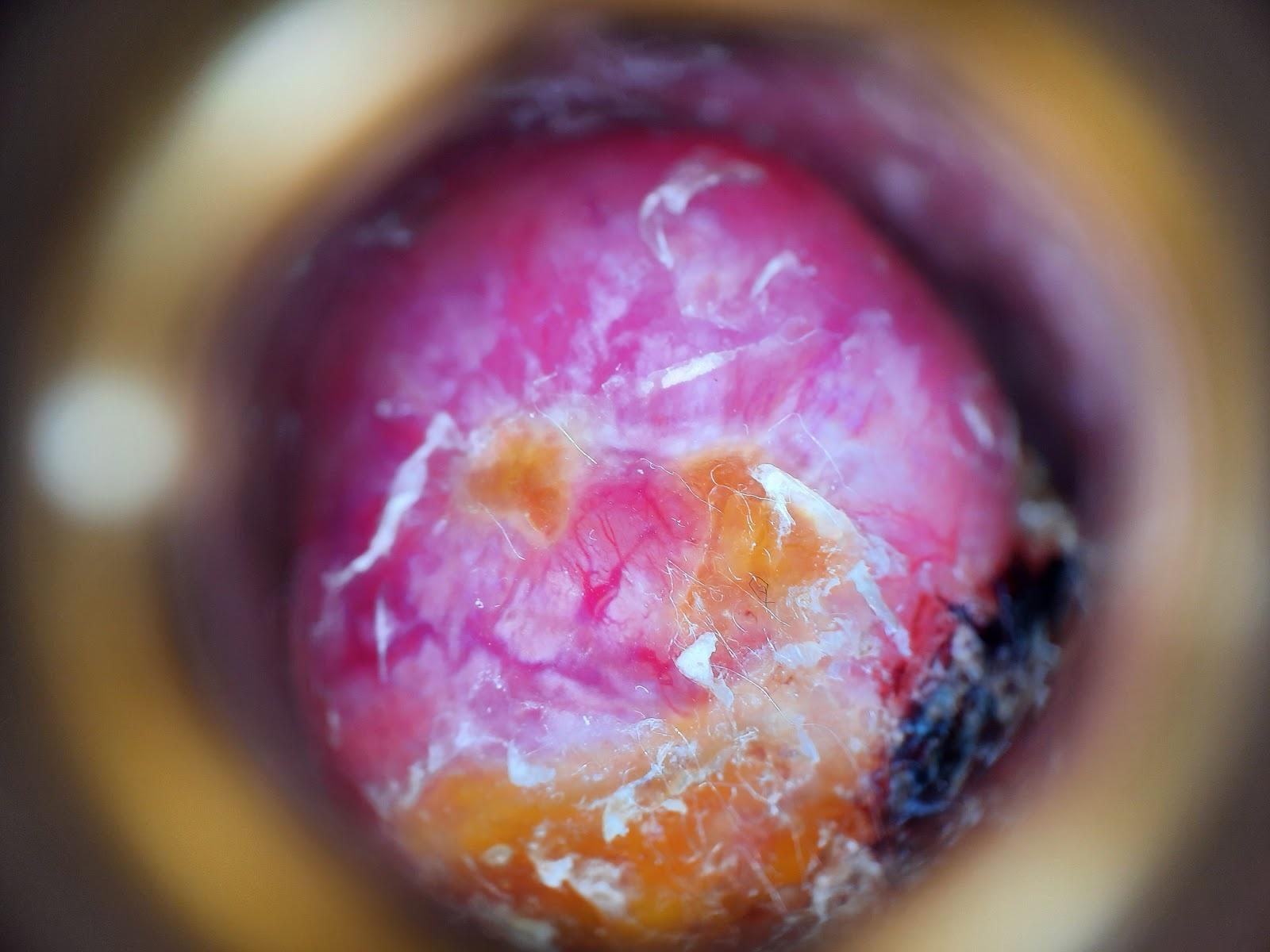Recorded as FST II. A male patient roughly 85 years of age or older. The lesion involves the anterior trunk. Histopathologically confirmed as a melanoma.